A dermatoscopic image of a skin lesion.
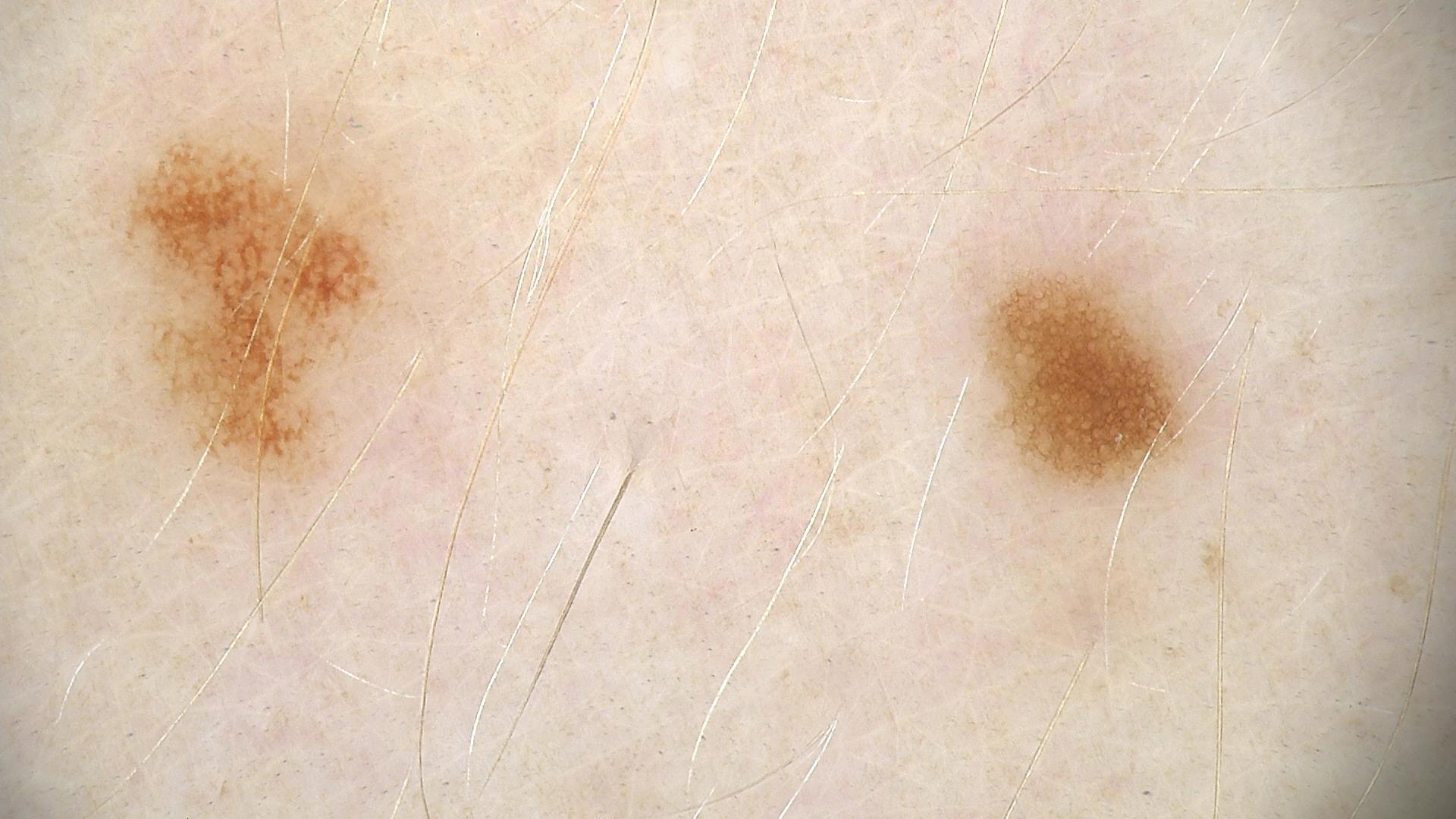Classified as a dysplastic junctional nevus.